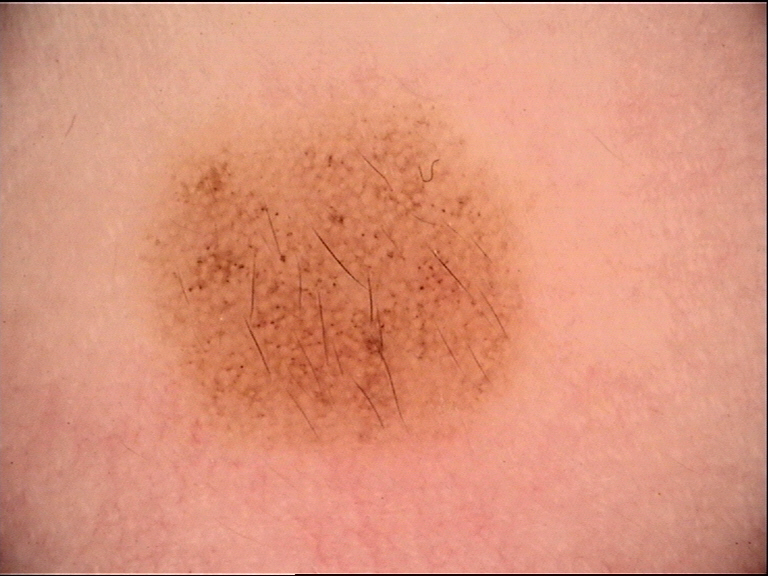Dermoscopy of a skin lesion.
The architecture is that of a banal lesion.
Consistent with a congenital junctional nevus.